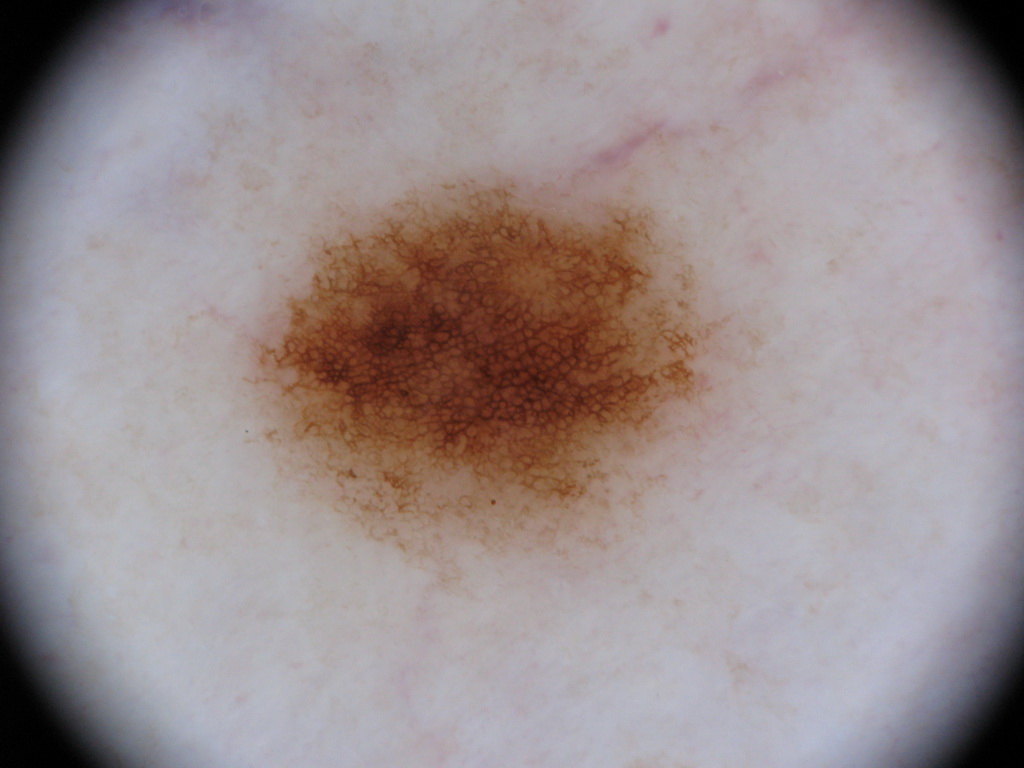| key | value |
|---|---|
| modality | dermoscopy |
| patient | female, in their 60s |
| lesion location | left=246, top=164, right=738, bottom=568 |
| dermoscopic findings | pigment network |
| lesion extent | ~19% of the field |
| diagnosis | a melanocytic nevus |